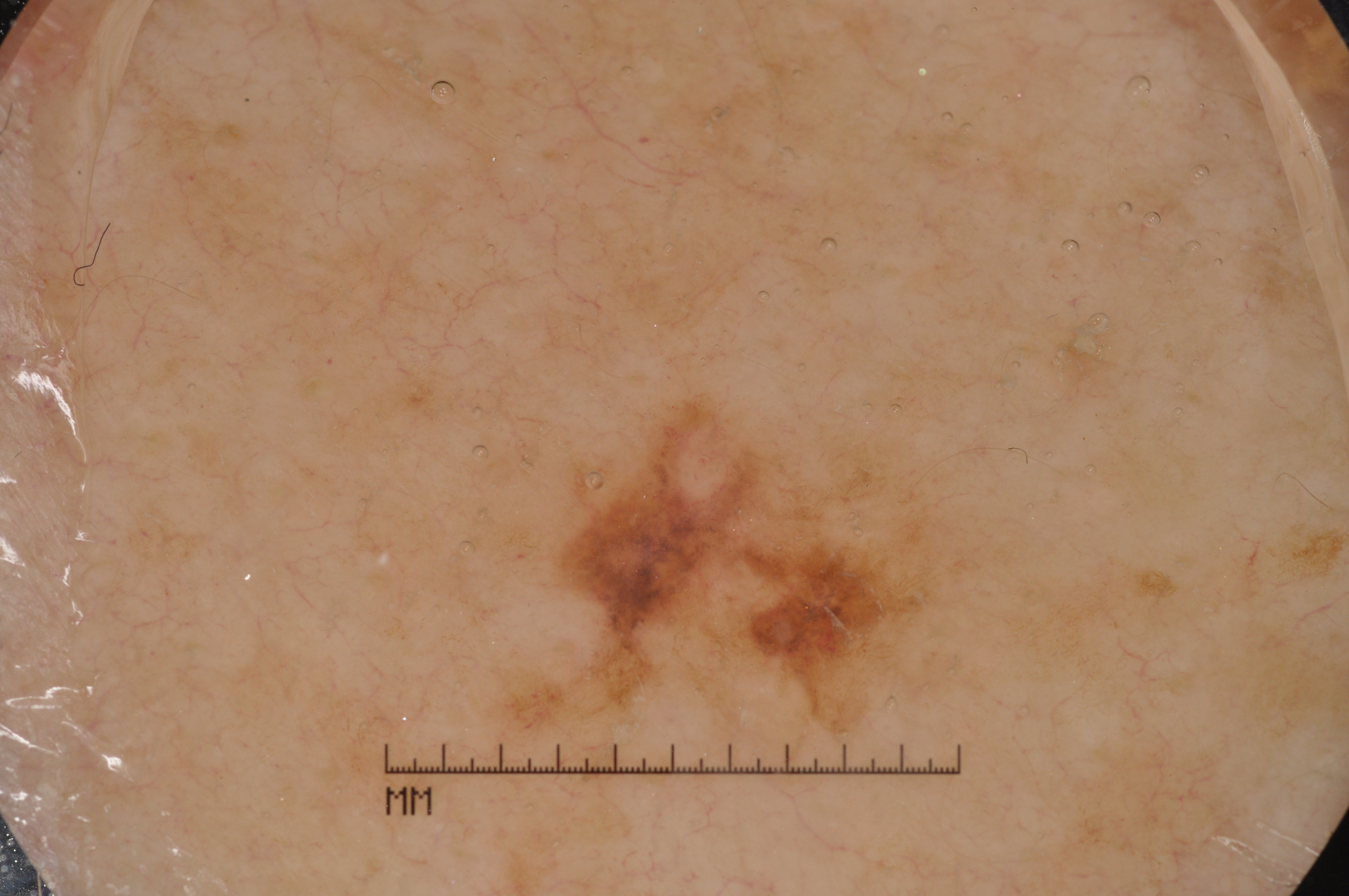patient — male, about 80 years old
imaging — dermatoscopic image of a skin lesion
bounding box — bbox(457, 379, 955, 763)
features — pigment network; absent: streaks, negative network, and milia-like cysts
diagnostic label — a melanoma, a skin cancer